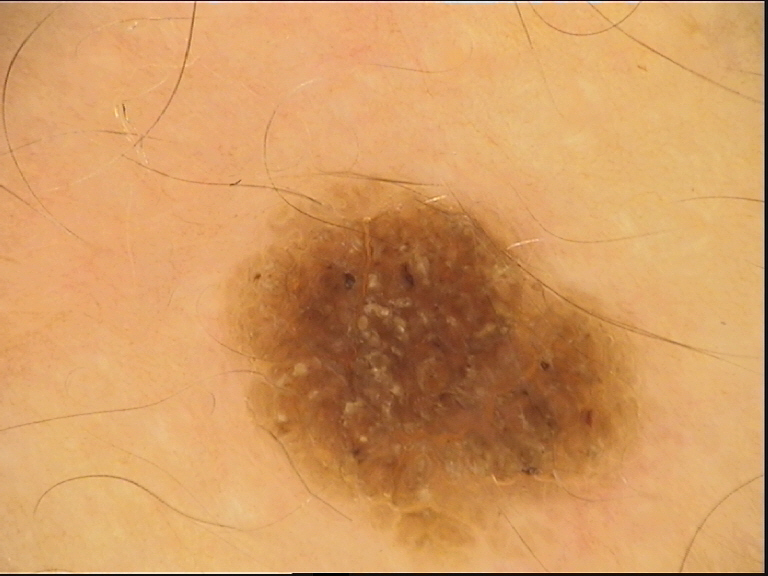• modality · dermoscopy
• classification · keratinocytic
• label · seborrheic keratosis (expert consensus)